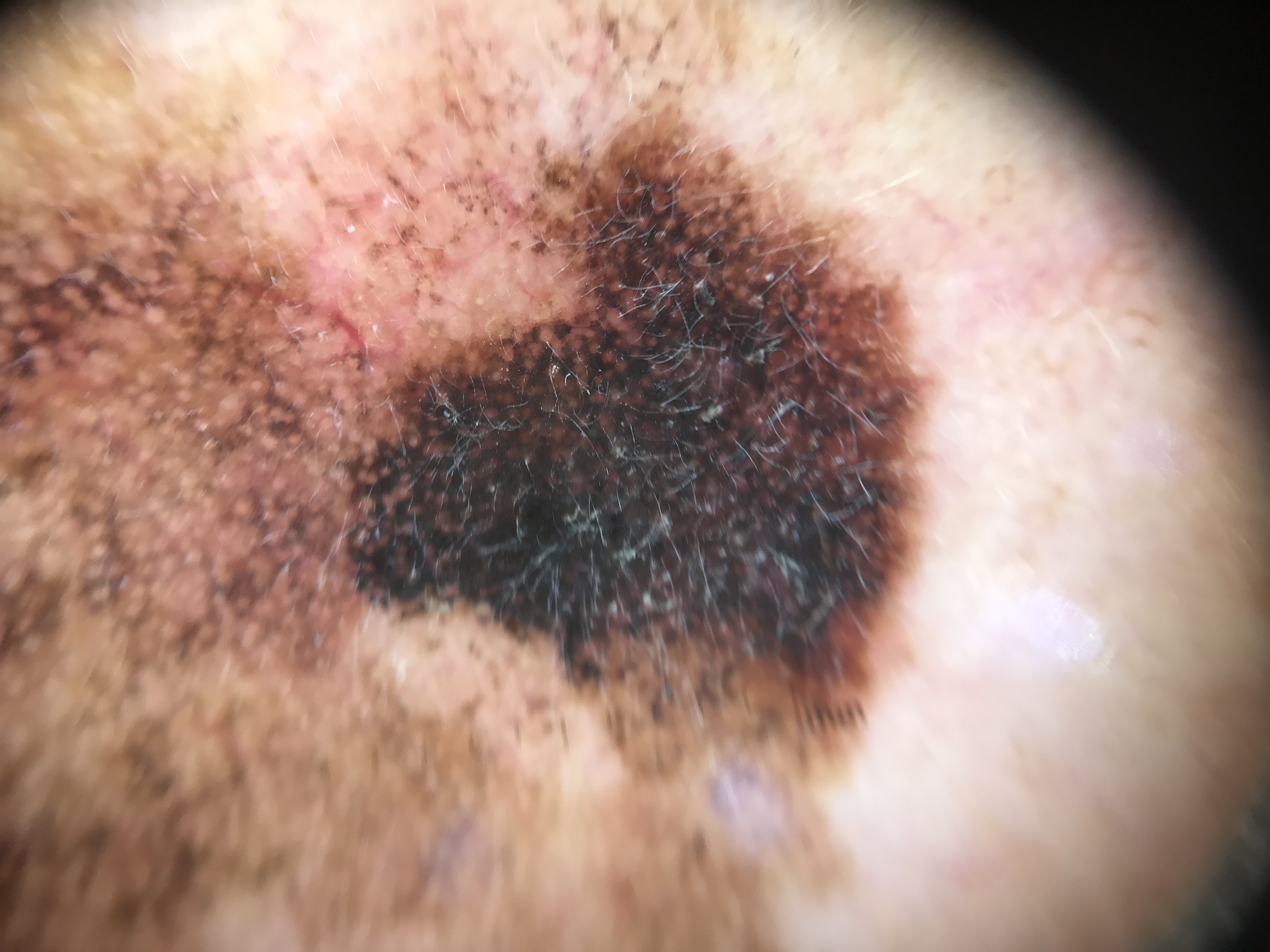| feature | finding |
|---|---|
| modality | dermatoscopy |
| diagnostic label | lentigo maligna (biopsy-proven) |